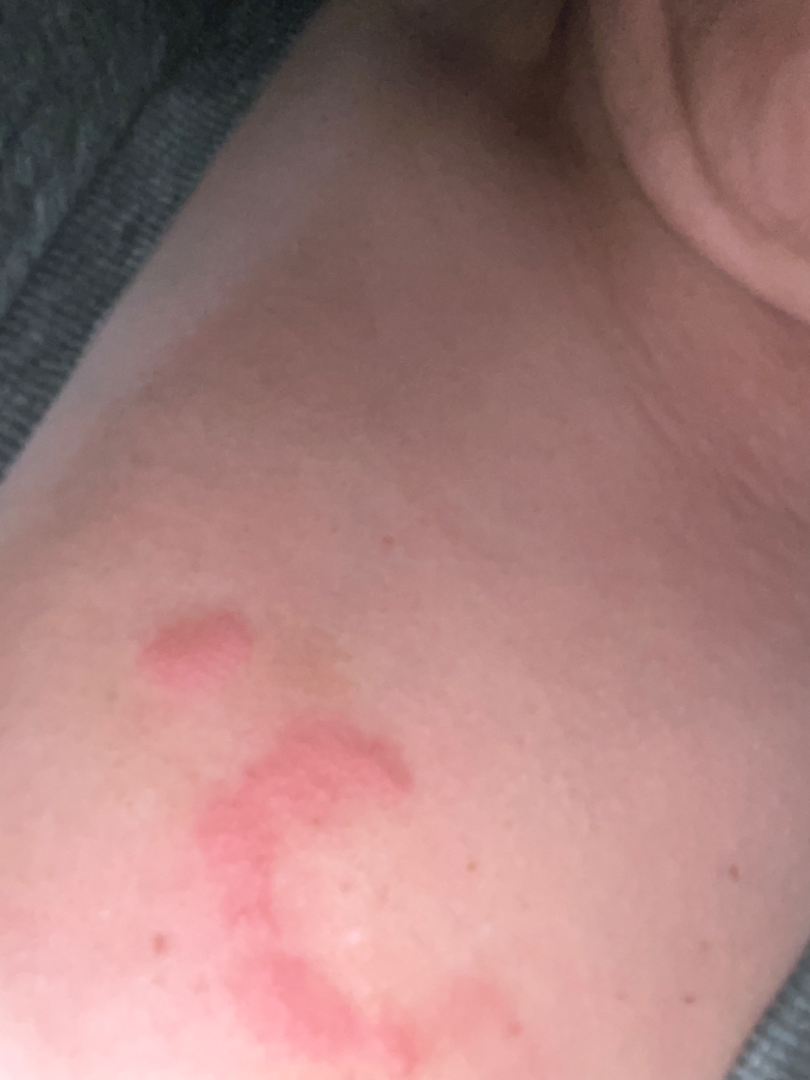History:
The patient reported no systemic symptoms. The patient considered this a rash. A close-up photograph. Present for one to three months. Symptoms reported: itching. The patient is 40–49, female.
Impression:
On photographic review by a dermatologist, the differential is split between Urticaria and Allergic Contact Dermatitis.